A dermoscopic photograph of a skin lesion: 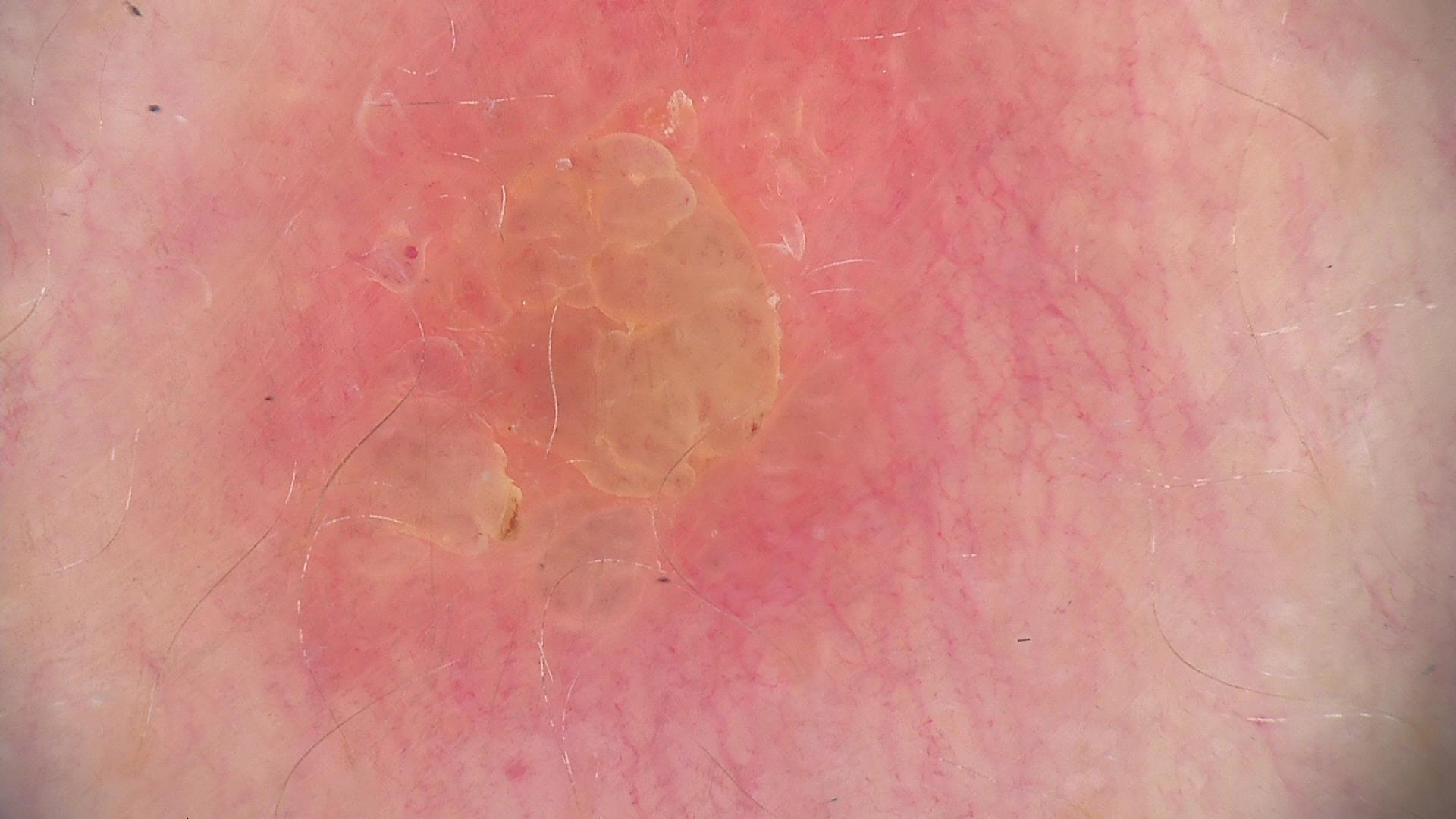The diagnosis was a banal lesion — a dermal nevus.